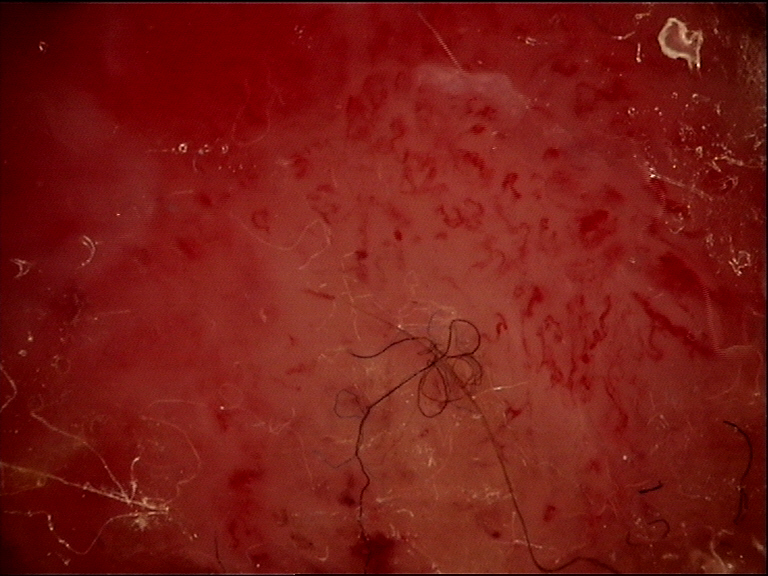Q: What kind of image is this?
A: dermoscopy
Q: How is the lesion classified?
A: keratinocytic
Q: What did the workup show?
A: squamous cell carcinoma (biopsy-proven)